The photograph was taken at an angle.
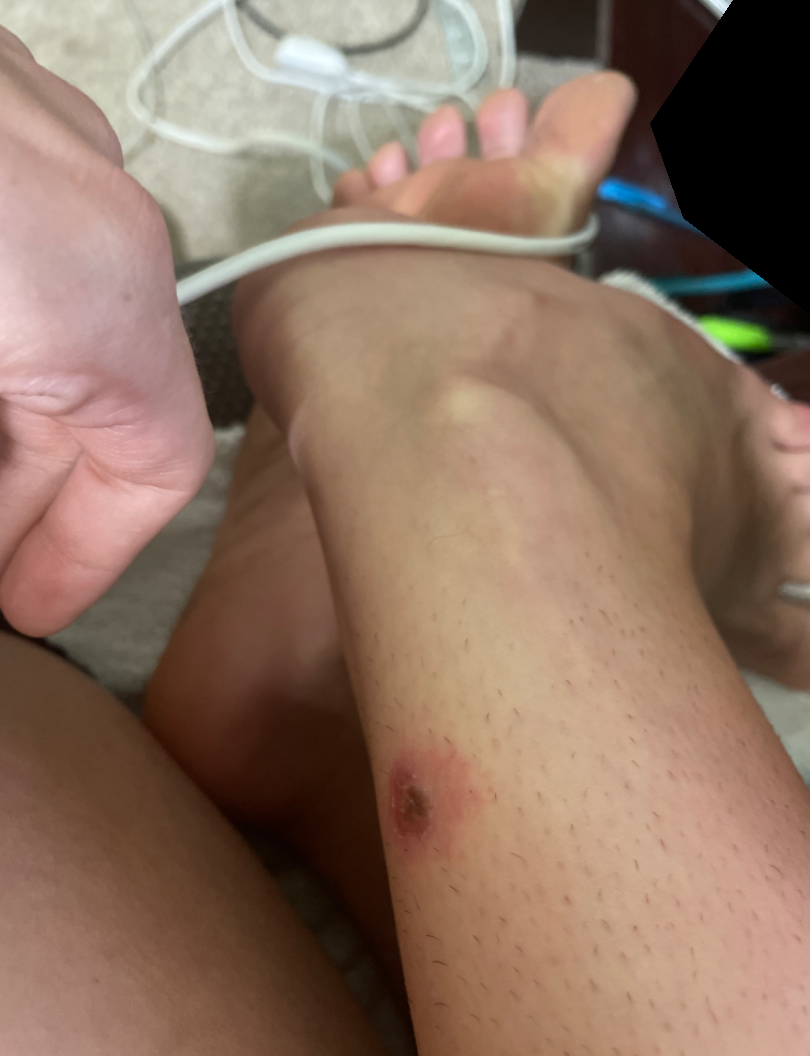The dermatologist could not determine a likely condition from the photograph alone.